The photo was captured at an angle. The lesion involves the leg. The subject is 30–39, female:
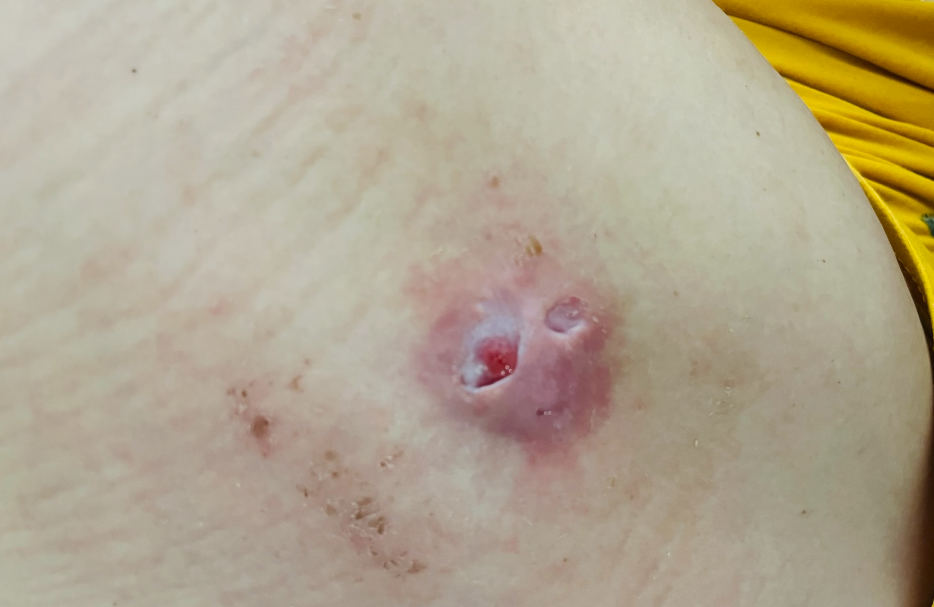history = three to twelve months
lesion symptoms = itching, burning, bothersome appearance and pain
surface texture = rough or flaky, fluid-filled and raised or bumpy
differential diagnosis = Hidradenitis (primary)